This image was taken at an angle.
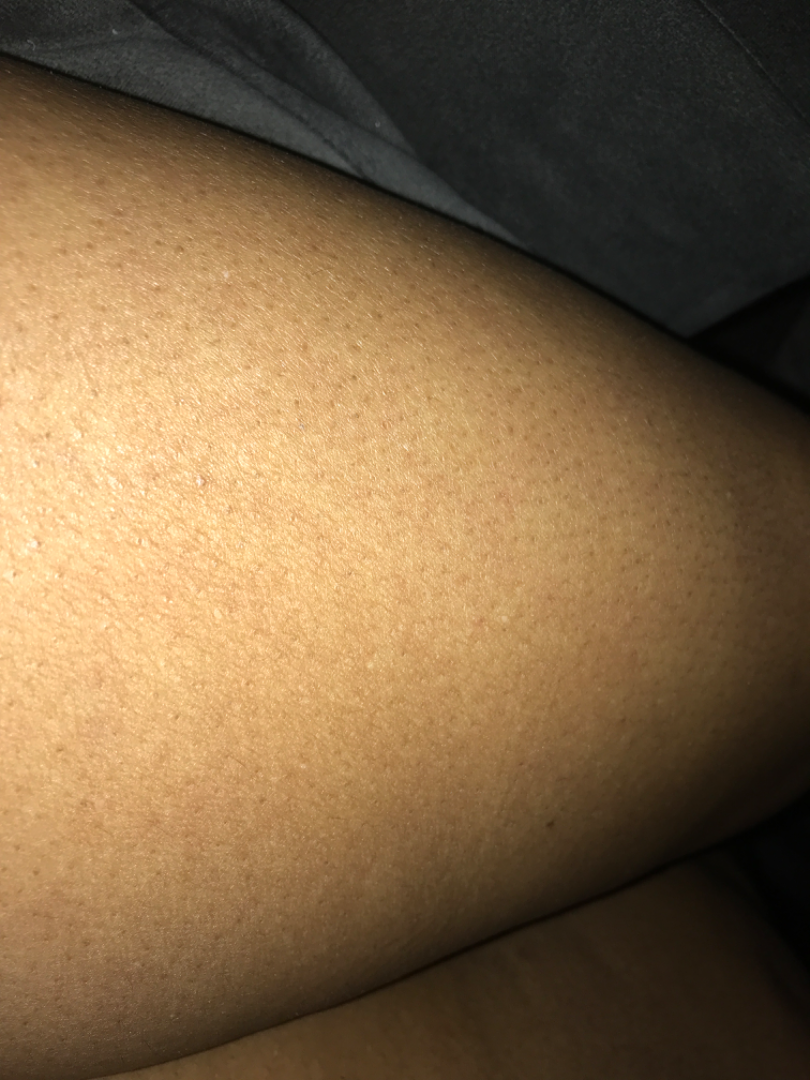{
  "assessment": "unable to determine"
}